Skin tone: non-clinician graders estimated Monk skin tone scale 1 (US pool) or 2 (India pool), the contributor notes bothersome appearance and itching, reported duration is one to four weeks, the photograph was taken at an angle, self-categorized by the patient as a rash — 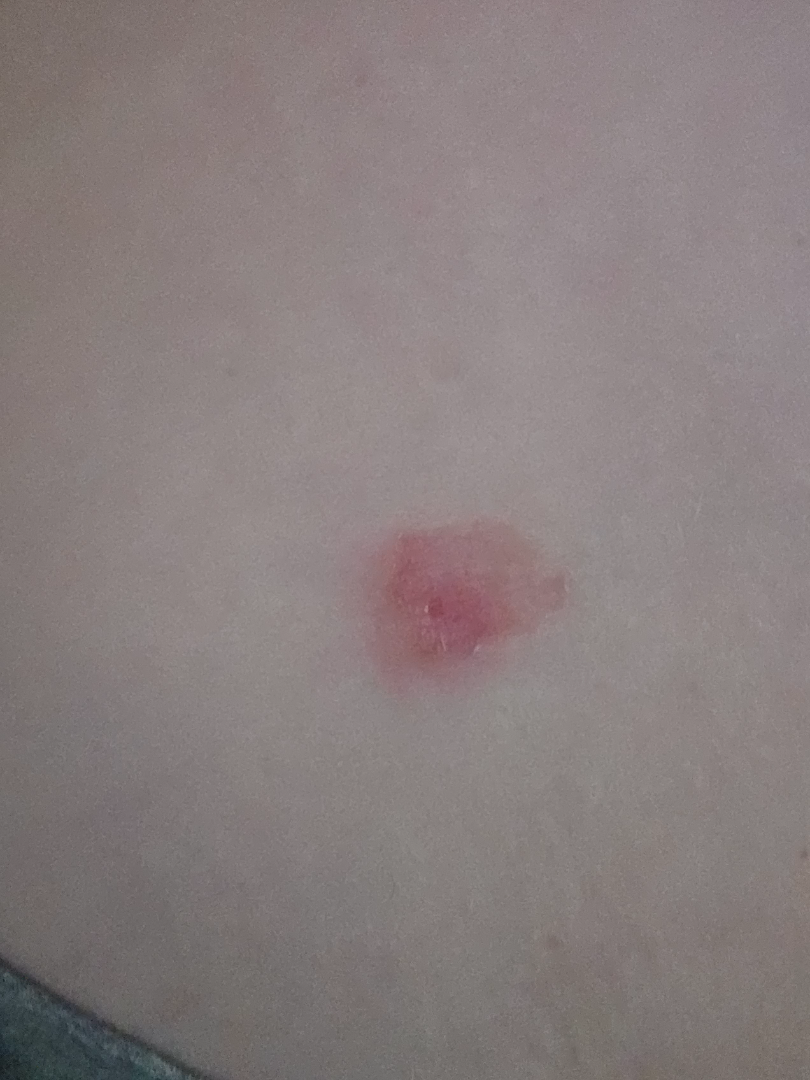Findings:
The skin condition could not be confidently assessed from this image.